Self-categorized by the patient as a rash; the lesion involves the arm and back of the hand; present for one to four weeks; the lesion is described as flat; female contributor, age 18–29; a close-up photograph: 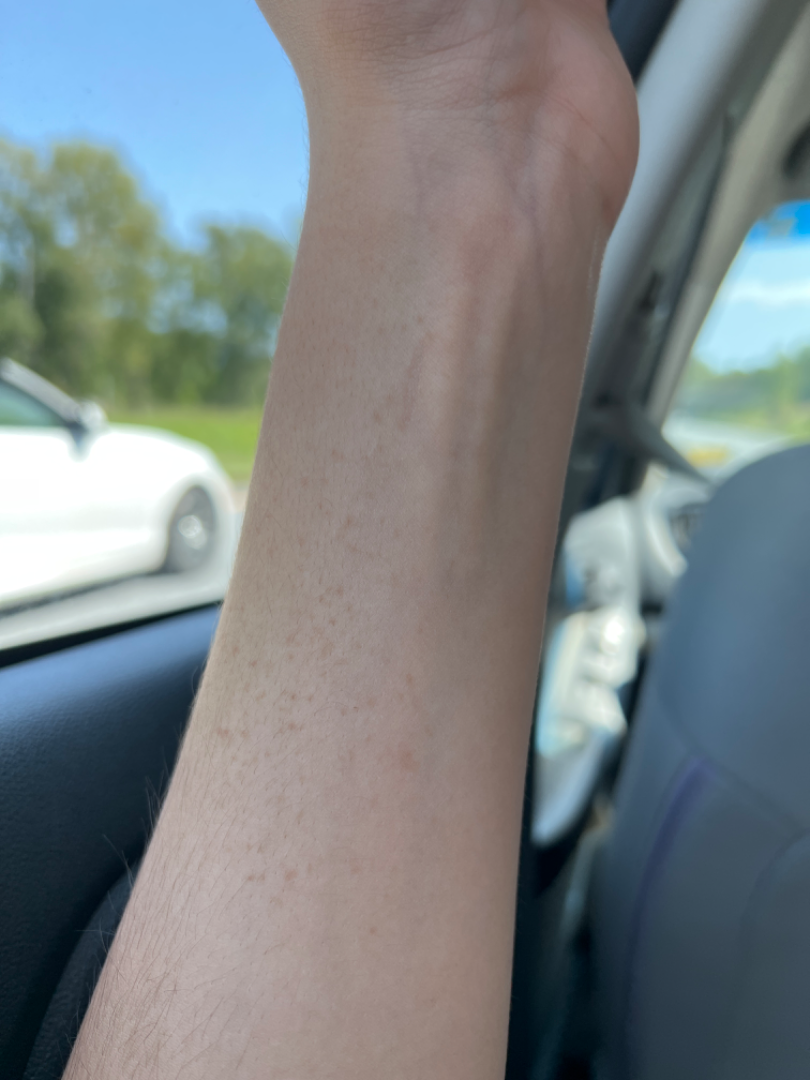On remote dermatologist review, Viral Exanthem, Hypersensitivity and Allergic Contact Dermatitis were each considered, in no particular order.